Self-categorized by the patient as a rash, texture is reported as raised or bumpy and rough or flaky, the condition has been present for less than one week, the lesion involves the arm, the photograph was taken at an angle, no relevant systemic symptoms: 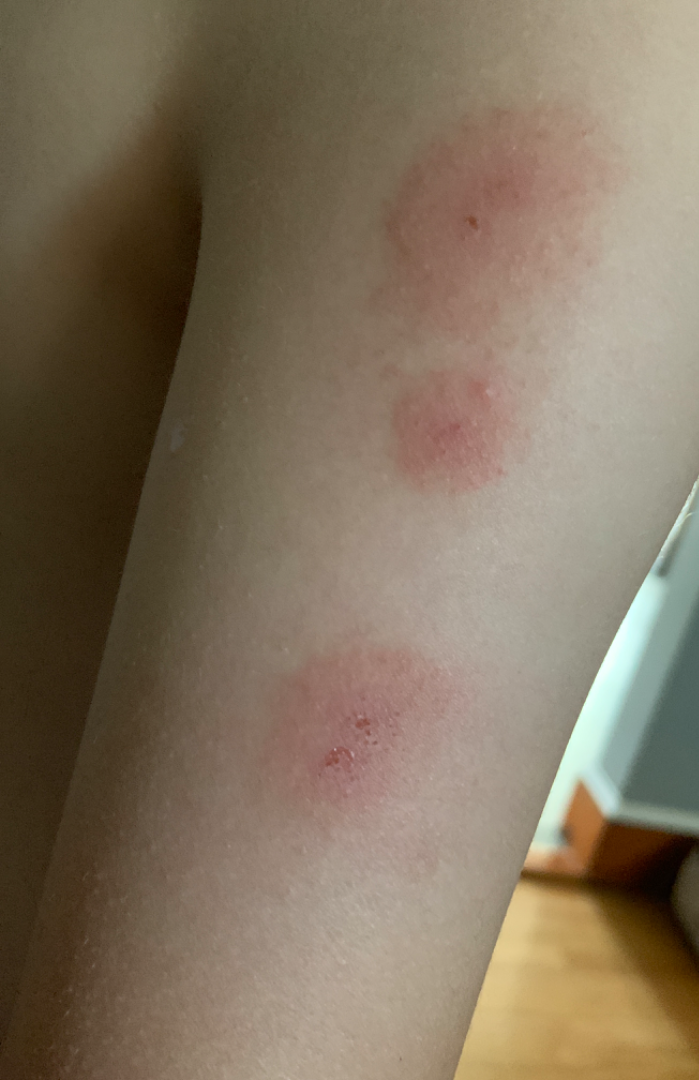On teledermatology review: the impression on review was Eczema.